A male subject in their mid-80s or older.
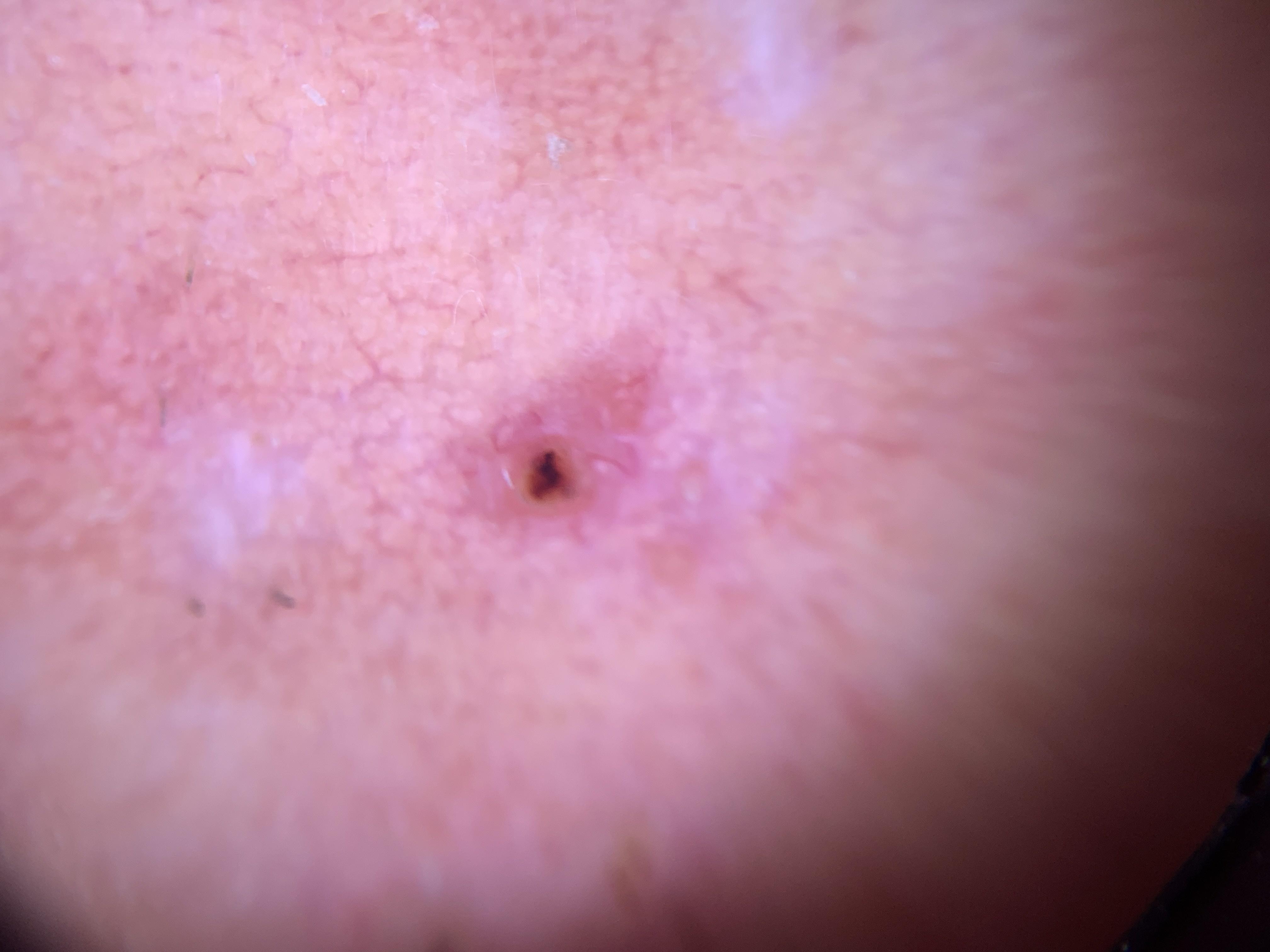pathology: Basal cell carcinoma (biopsy-proven).